The photograph was taken at an angle — 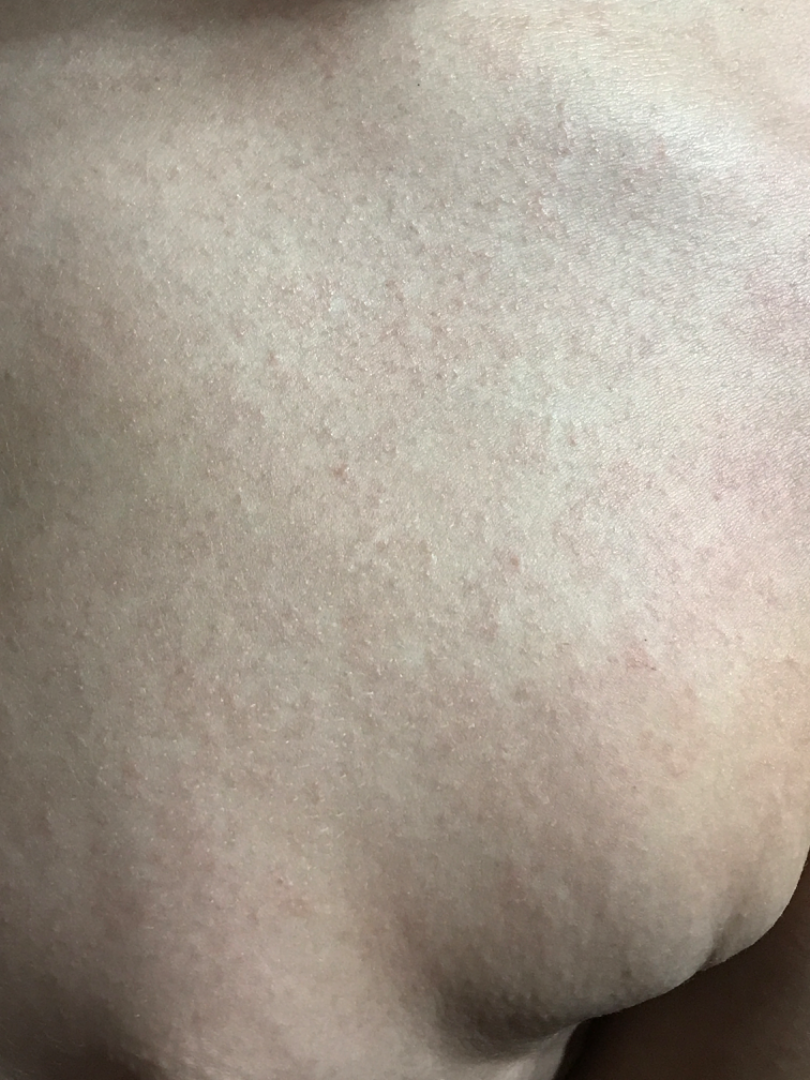Case summary:
– dermatologist impression — Miliaria (favored)